The affected area is the arm. The contributor is 18–29, male. The photograph was taken at an angle: 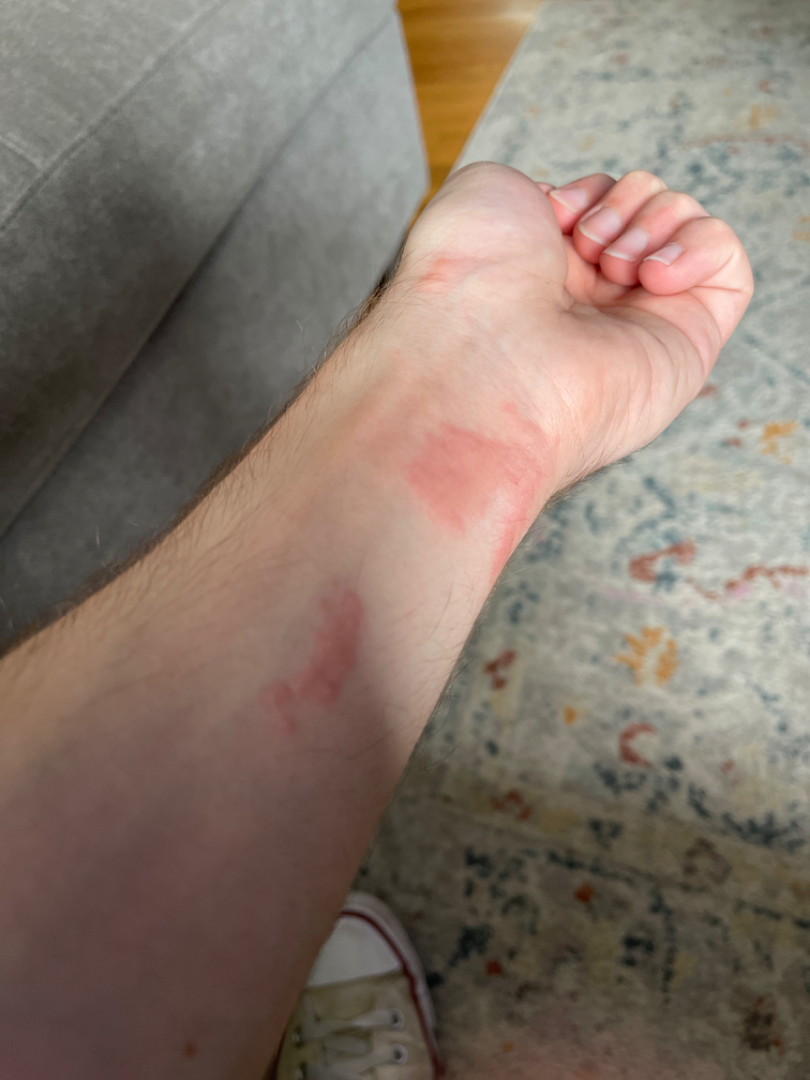The patient considered this a rash.
Texture is reported as raised or bumpy.
Fitzpatrick phototype II.
Reported duration is less than one week.
No relevant systemic symptoms.
The primary impression is Allergic Contact Dermatitis; possibly Urticaria; with consideration of Insect Bite.